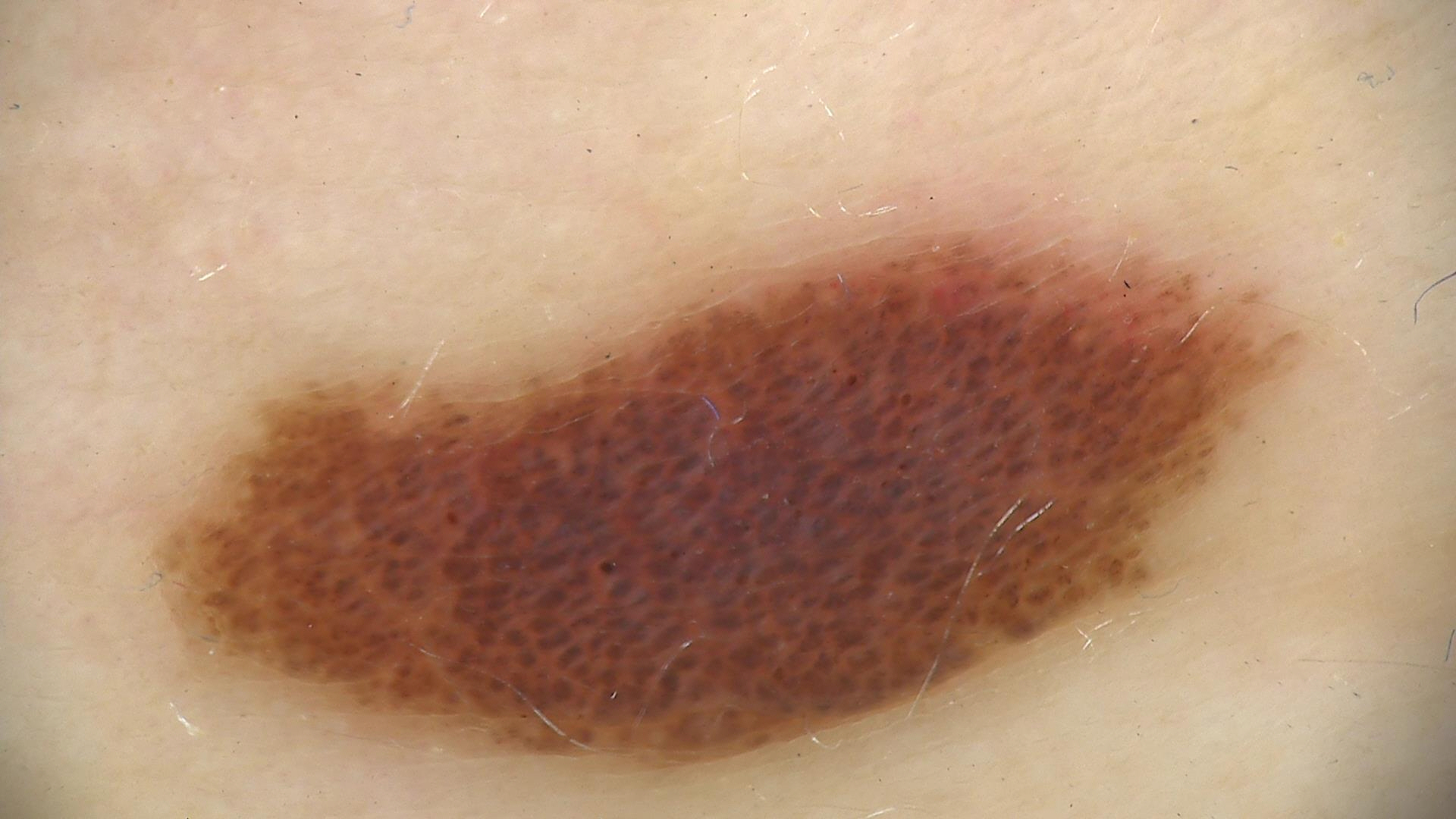Summary: This is a banal lesion. Impression: Classified as a compound nevus.